The lesion involves the front of the torso · the subject is 30–39, female · the patient indicates the lesion is raised or bumpy · symptoms reported: itching · the patient also reports fatigue · an image taken at an angle · present for about one day · self-categorized by the patient as a rash.
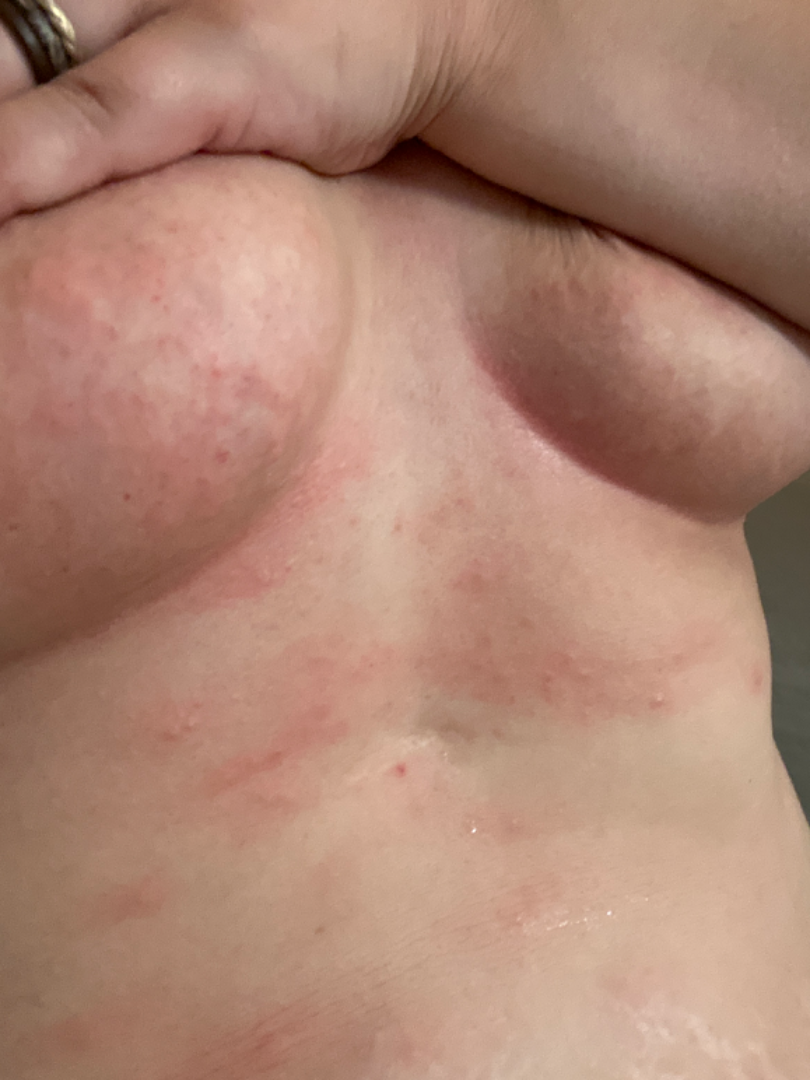The condition could not be reliably identified from the image.